The lesion involves the arm and leg · the photo was captured at a distance:
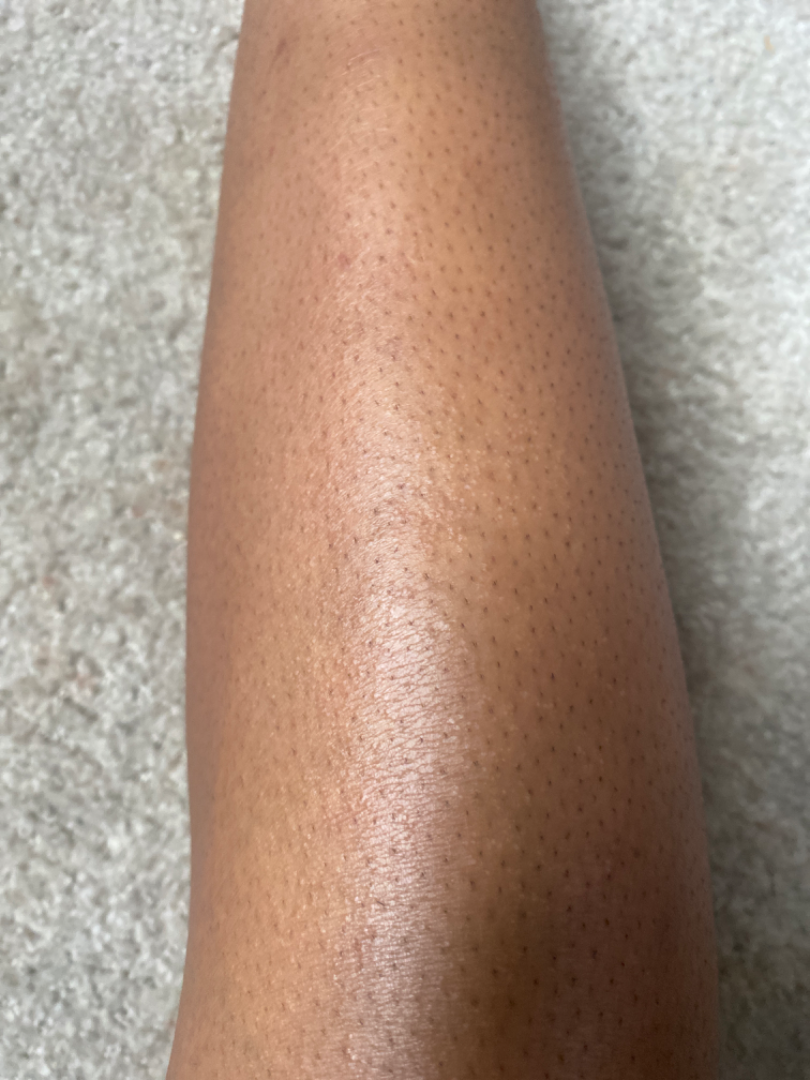symptoms = none reported | constitutional symptoms = joint pain | surface texture = raised or bumpy | impression = Eczema and Xerosis were considered with similar weight.